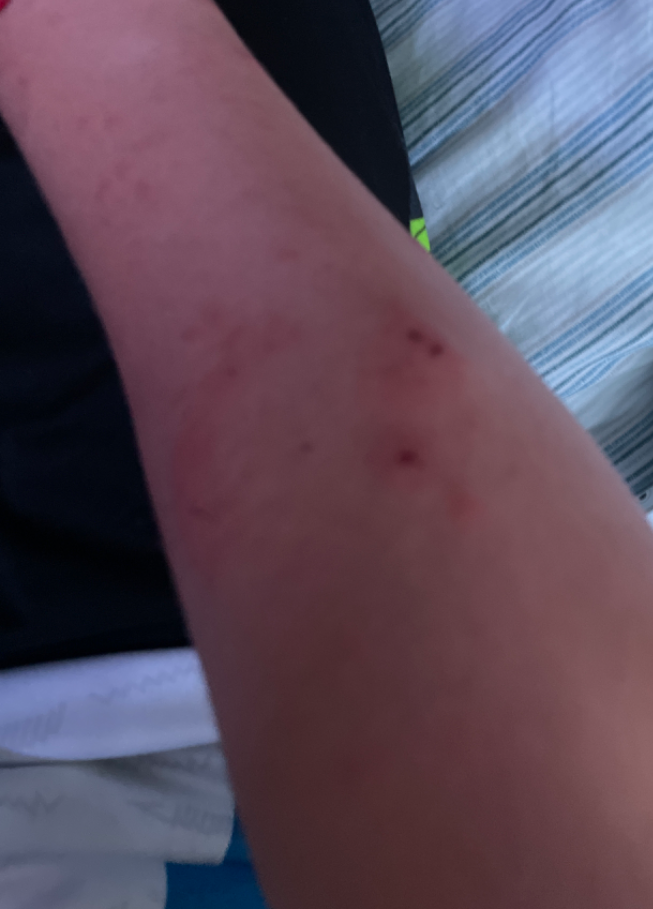History:
Fitzpatrick phototype III; non-clinician graders estimated 2 on the Monk Skin Tone. A close-up photograph.
Impression:
The reviewing clinician's impression was: Allergic Contact Dermatitis (0.67); Eczema (0.33).